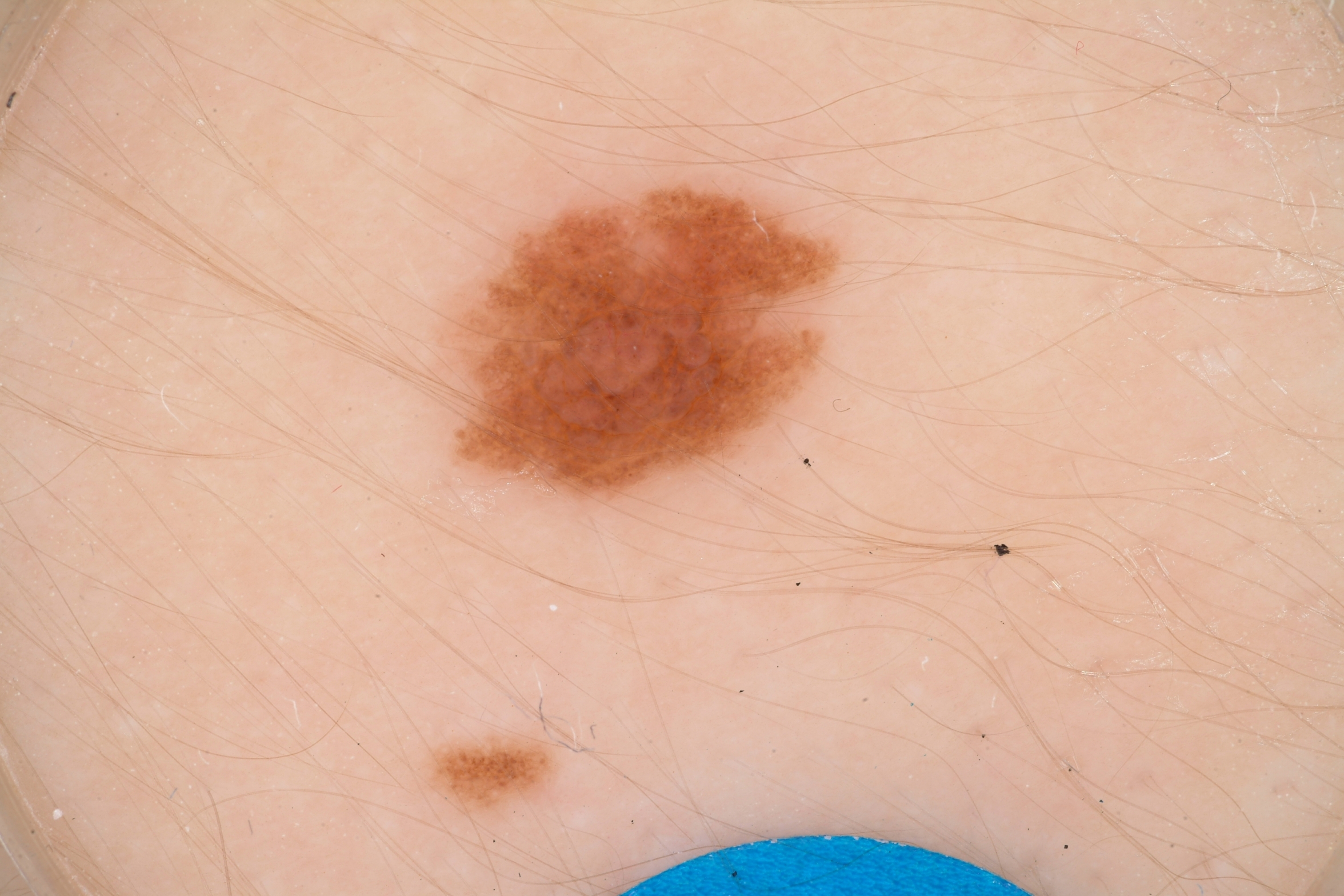Findings:
– patient — male, aged approximately 15
– image — dermoscopic image
– lesion location — [443,183,849,501]
– features — milia-like cysts; absent: streaks, globules, negative network, and pigment network
– lesion extent — ~8% of the field
– diagnostic label — a melanocytic nevus, a benign lesion